A dermoscopic view of a skin lesion. A male patient aged approximately 45 — 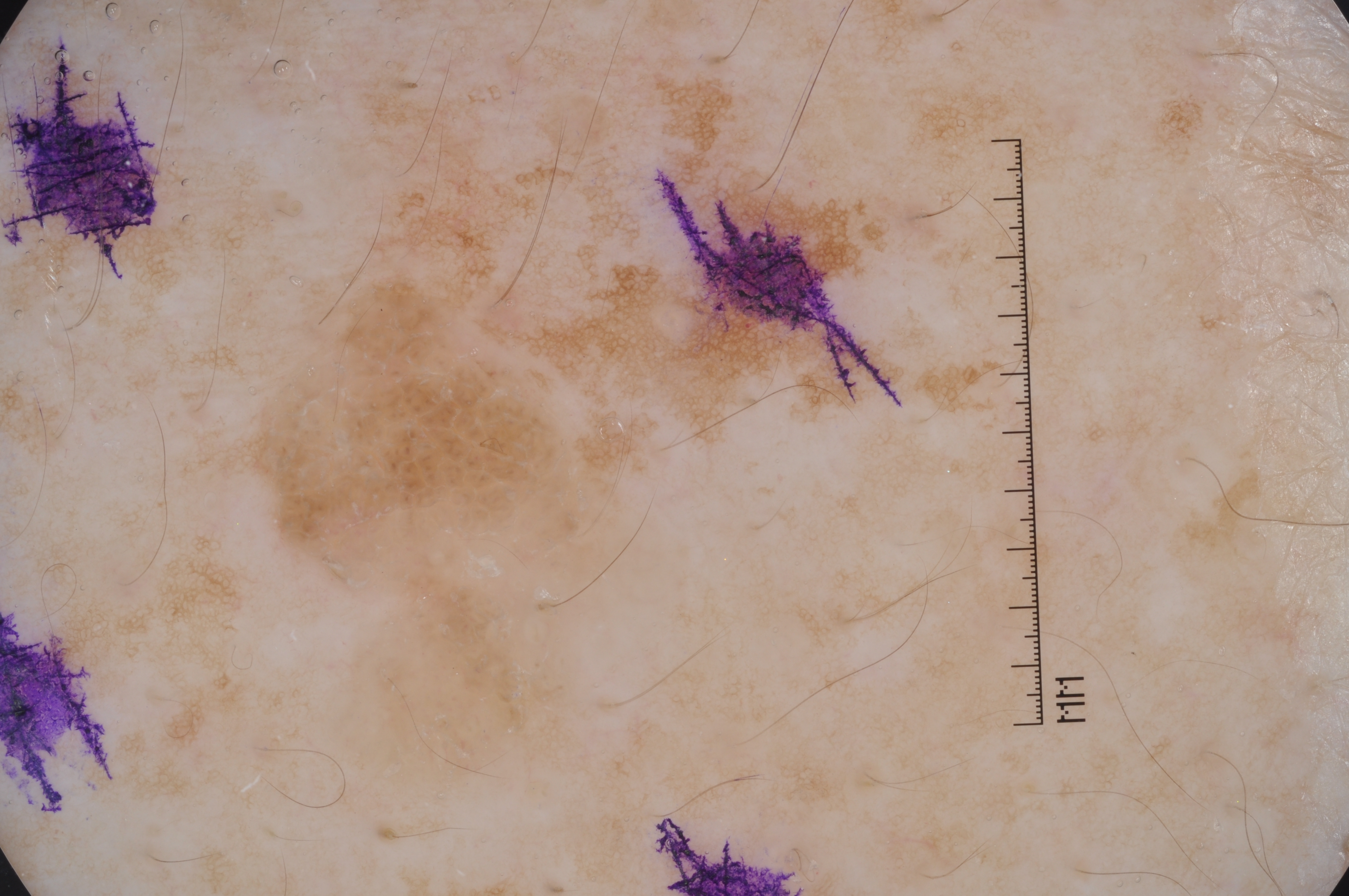dermoscopic findings = negative network; lesion bbox = x1=21, y1=7, x2=1047, y2=888; lesion extent = large; assessment = a seborrheic keratosis, a non-melanocytic (keratinocytic) lesion.